A dermoscopy image of a single skin lesion.
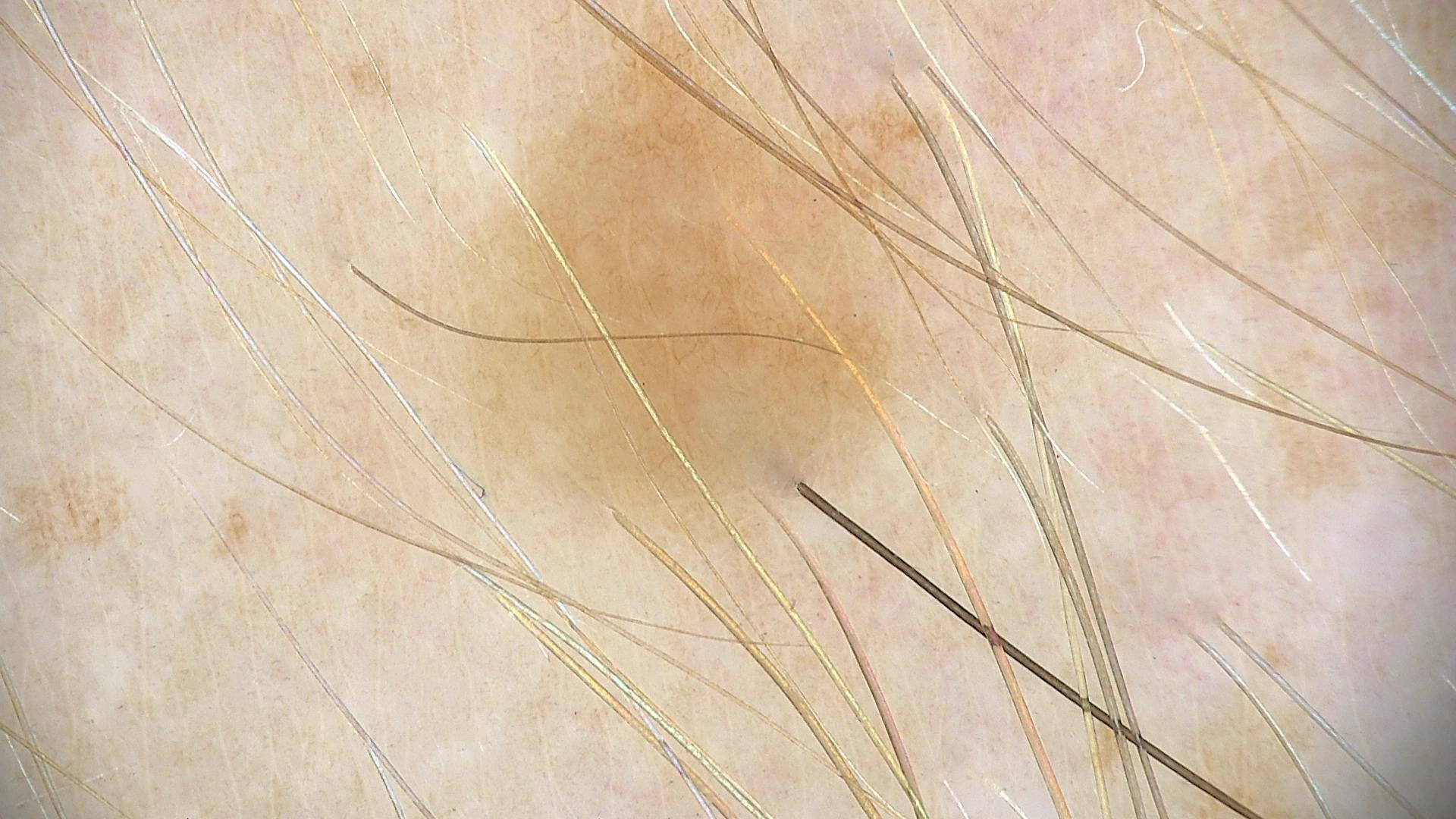The architecture is that of a banal lesion.
Classified as a dermal nevus.